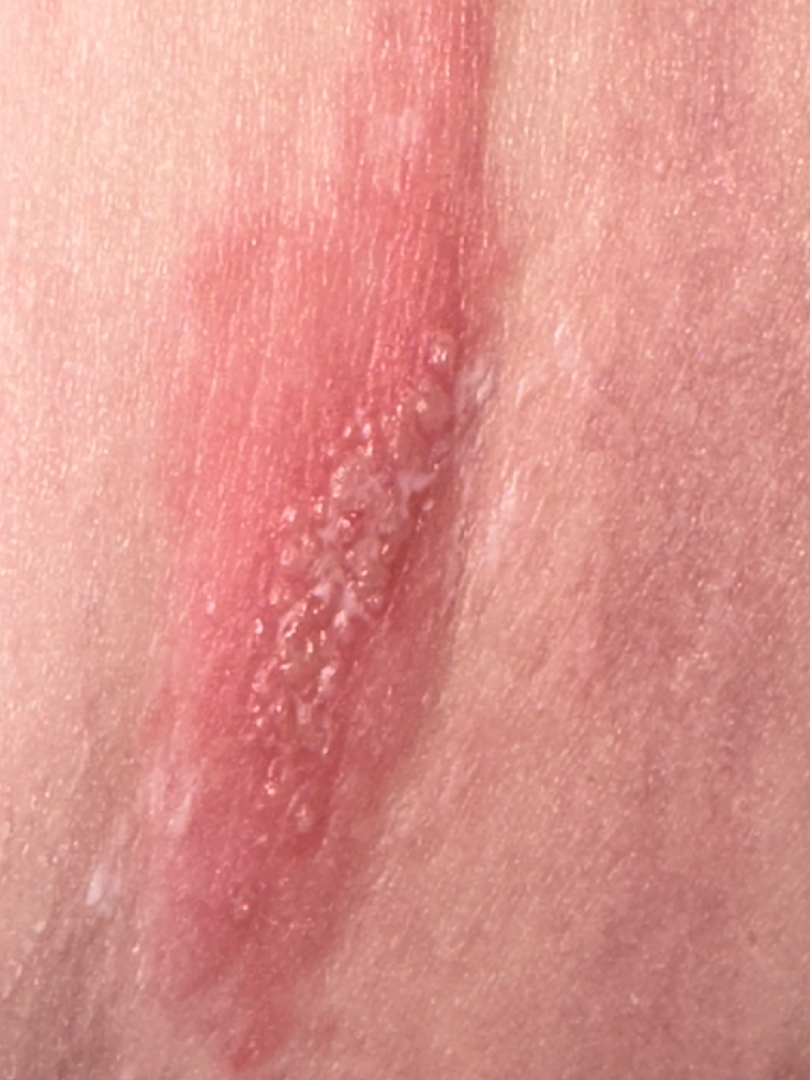Background:
The patient reported no systemic symptoms. The contributor is 30–39, male. The lesion is described as raised or bumpy. The photograph is a close-up of the affected area. The condition has been present for about one day. Reported lesion symptoms include itching and burning. The patient considered this a rash.
Findings:
On remote review of the image, Herpes Simplex (favored); Herpes Zoster (considered).